Female patient, age 30–39 · the photograph is a close-up of the affected area · the affected area is the leg: 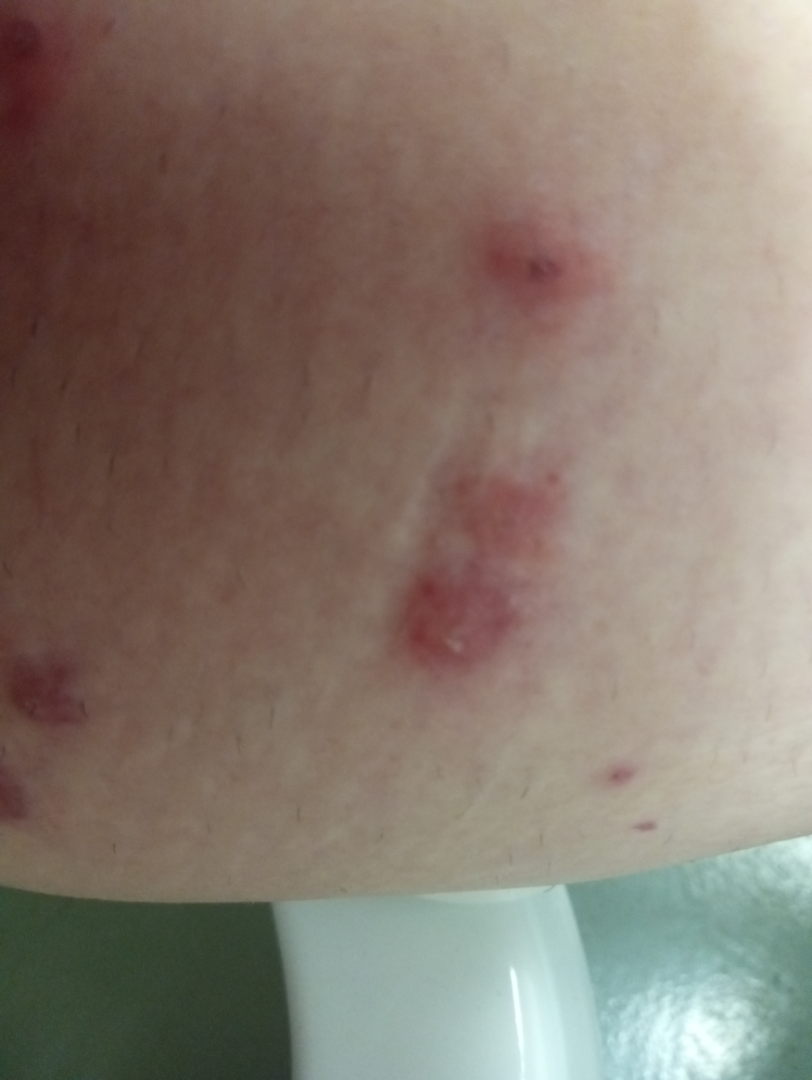Impression:
The case was difficult to assess from the available photograph.
History:
No constitutional symptoms were reported. Reported duration is less than one week. Texture is reported as raised or bumpy and fluid-filled. Symptoms reported: itching, enlargement and burning. Self-categorized by the patient as a rash.